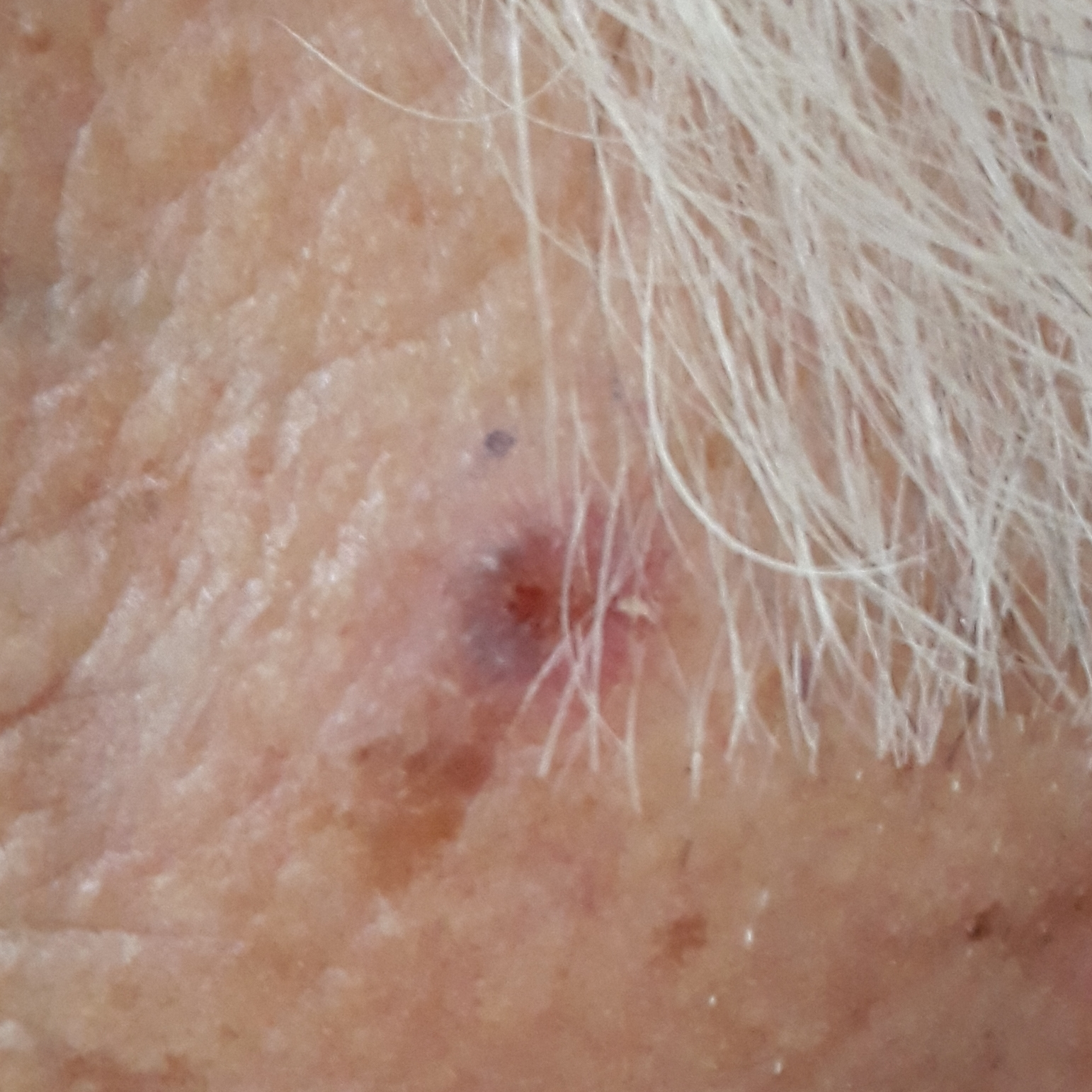modality = smartphone clinical photo | reported symptoms = elevation, bleeding, itching | pathology = basal cell carcinoma (biopsy-proven).